A dermoscopic image of a skin lesion.
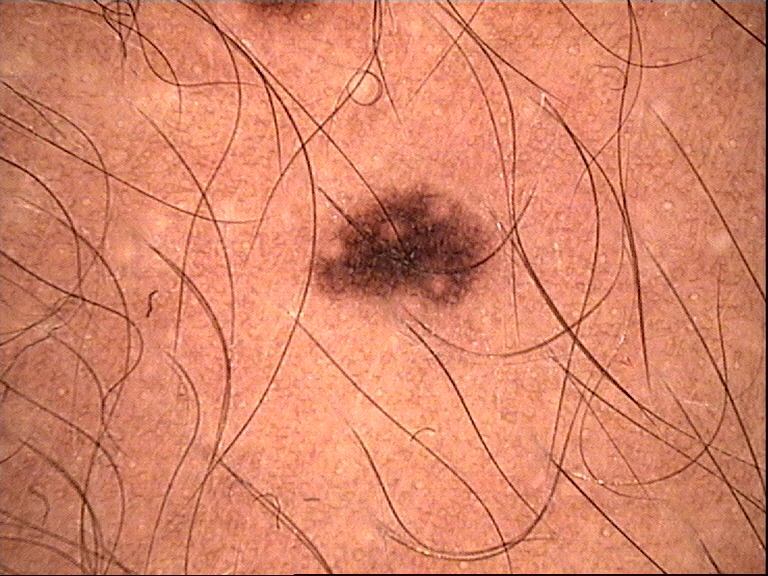label: dysplastic junctional nevus (expert consensus).